This is a close-up image · female contributor, age 18–29:
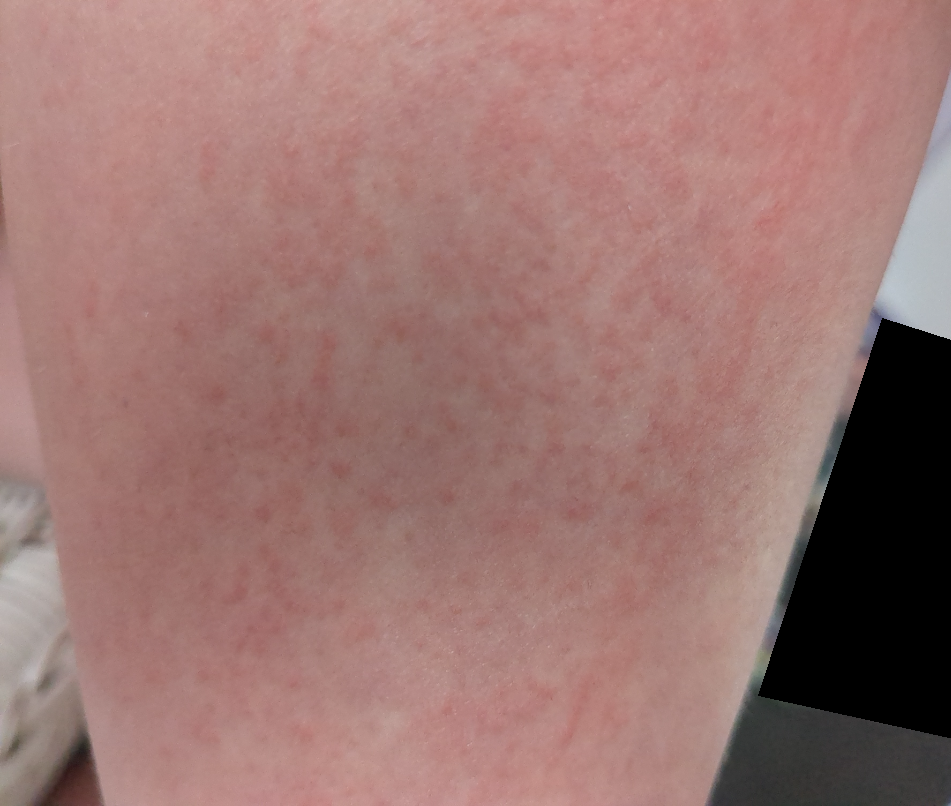The condition could not be reliably identified from the image.